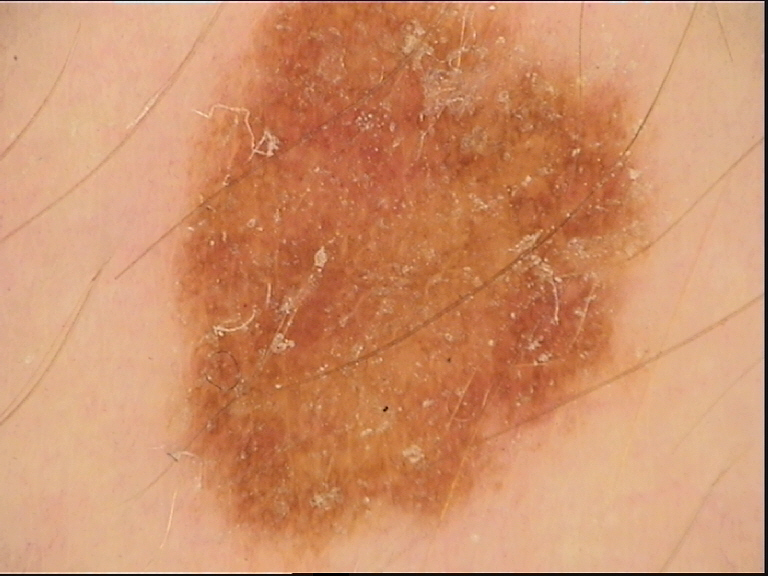Consistent with a dysplastic compound nevus.